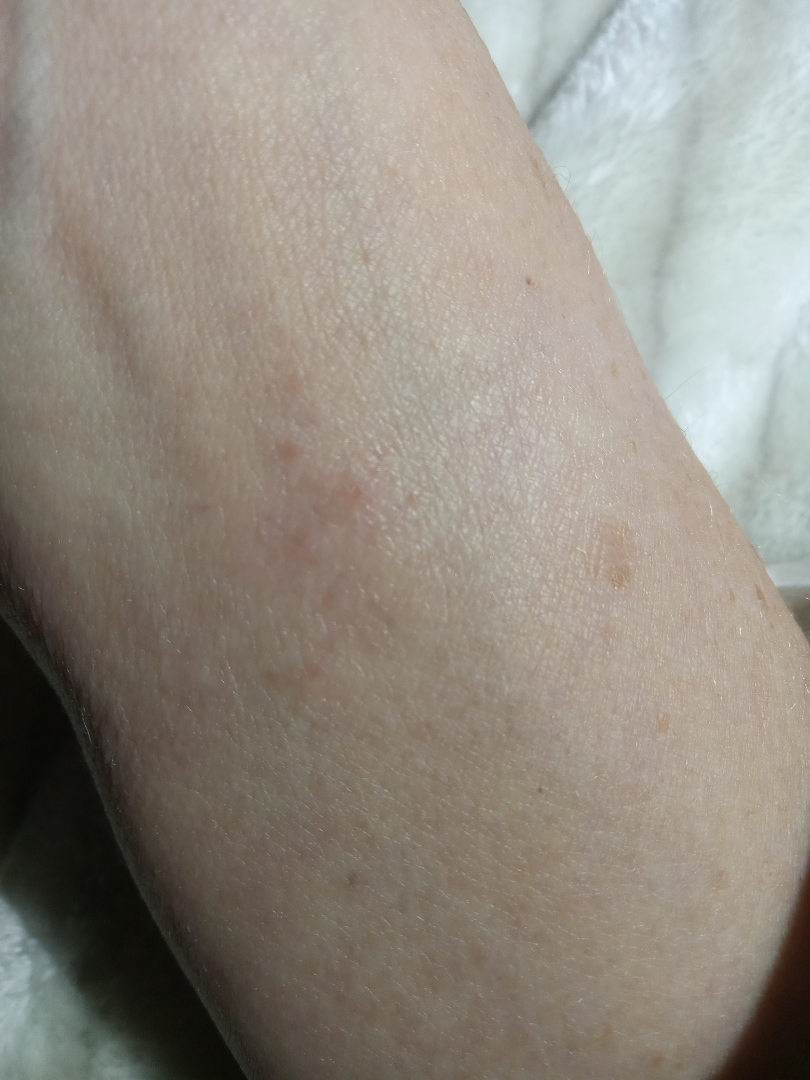patient describes the issue as=a rash | lesion symptoms=itching and burning | affected area=head or neck and arm | onset=less than one week | subject=female, age 50–59 | systemic symptoms=joint pain and fatigue | shot type=close-up | impression=Eczema (possible); Hypersensitivity (possible); Allergic Contact Dermatitis (possible).